Dermoscopy of a skin lesion:
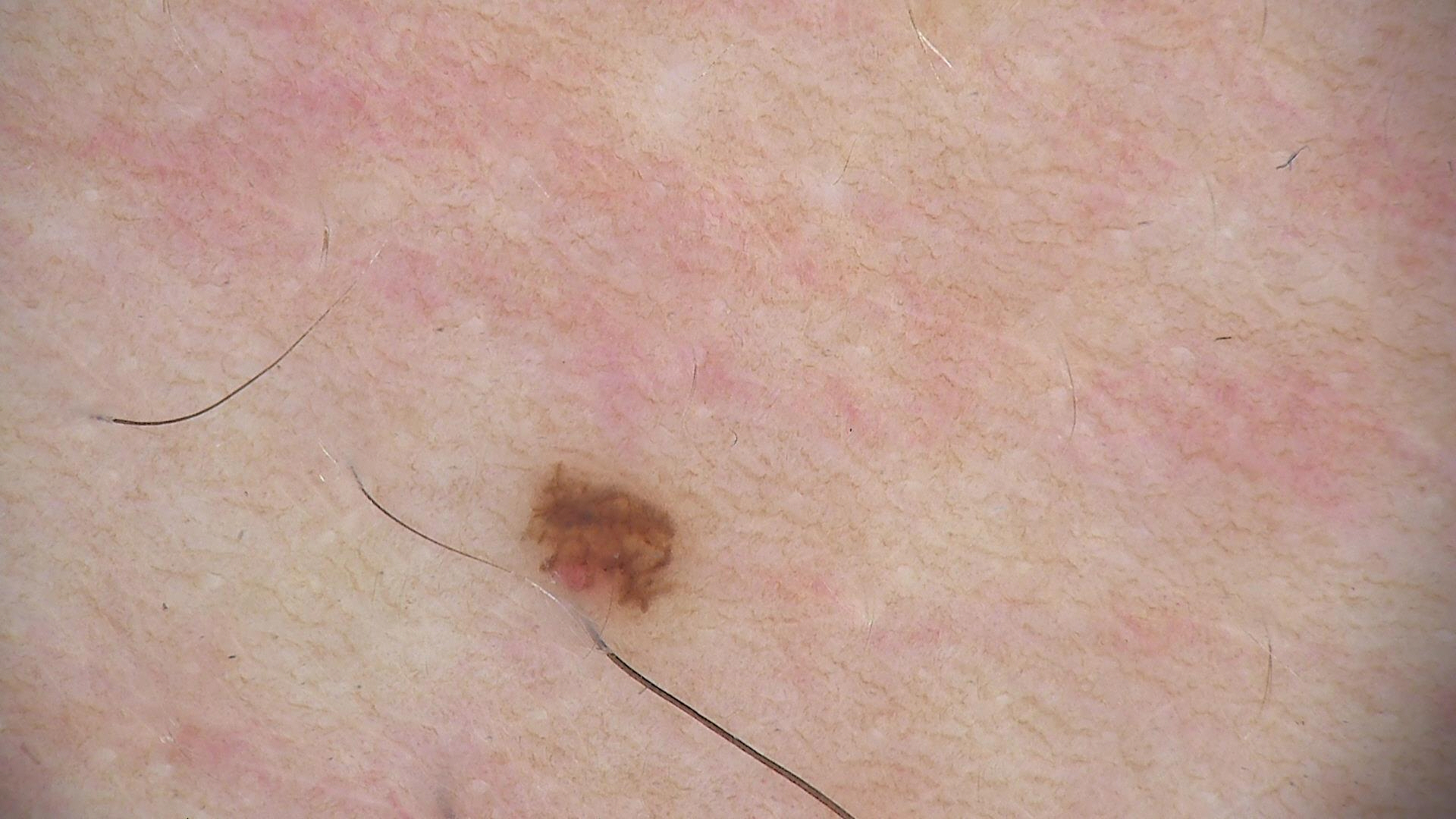diagnosis: dysplastic junctional nevus (expert consensus).